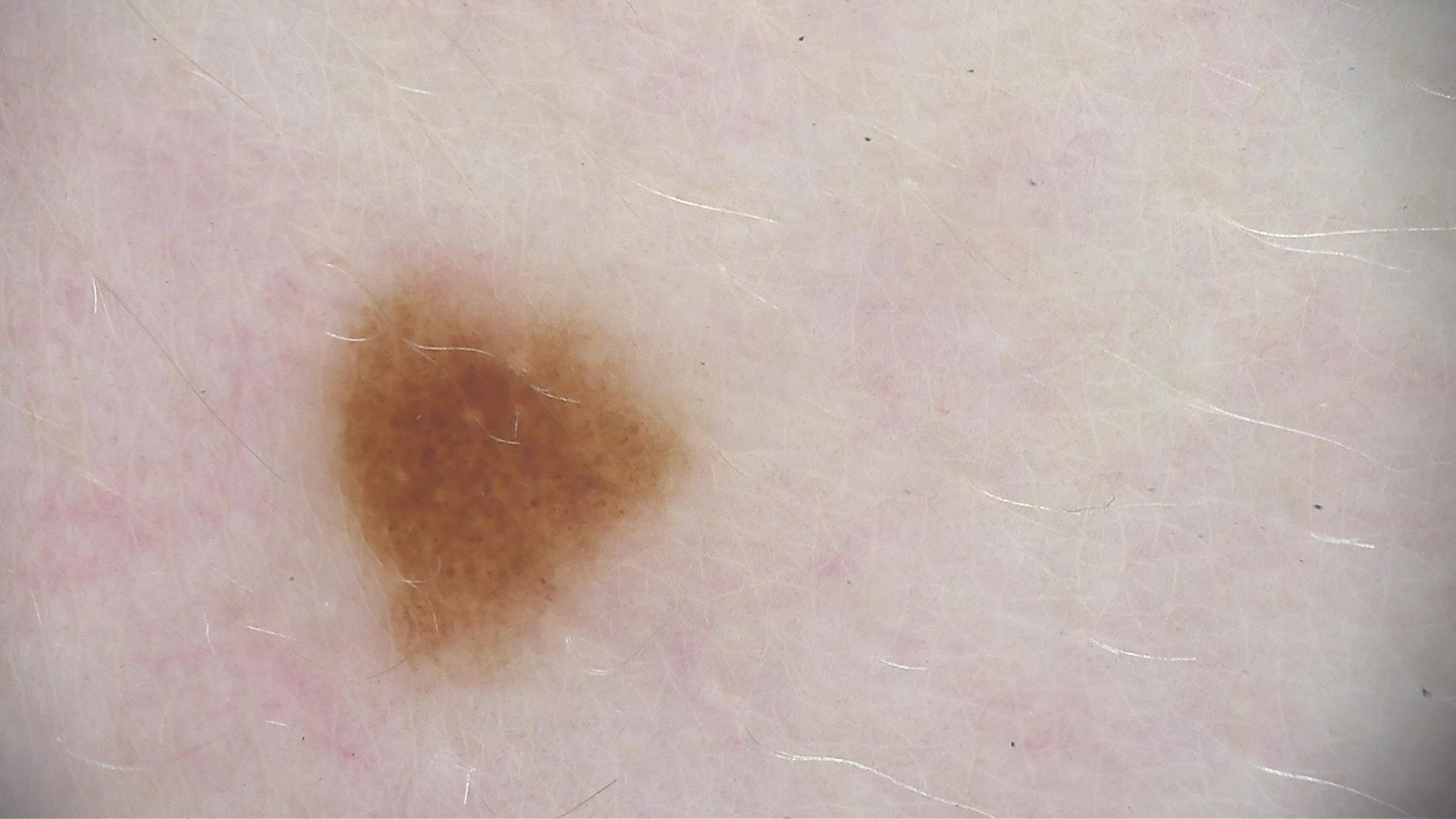{
  "image": "dermatoscopy",
  "lesion_type": {
    "main_class": "banal",
    "pattern": "compound"
  },
  "diagnosis": {
    "name": "compound nevus",
    "code": "cb",
    "malignancy": "benign",
    "super_class": "melanocytic",
    "confirmation": "expert consensus"
  }
}